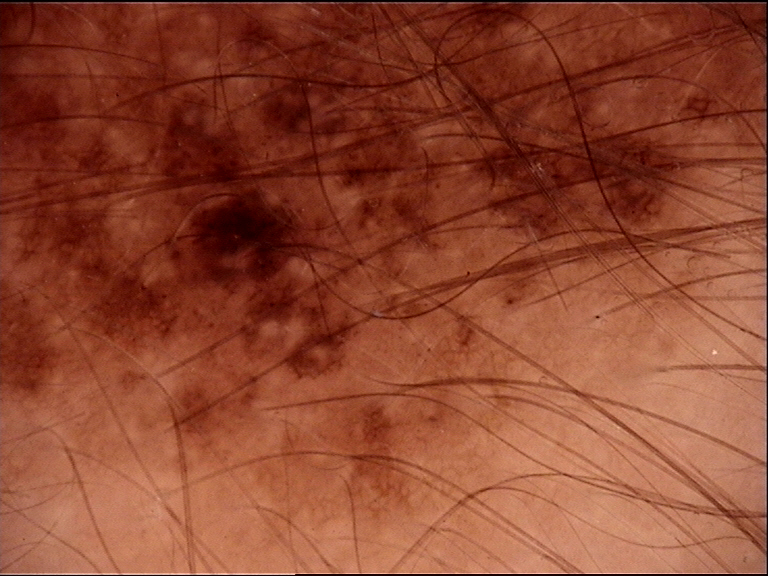The diagnosis was a congenital junctional nevus.